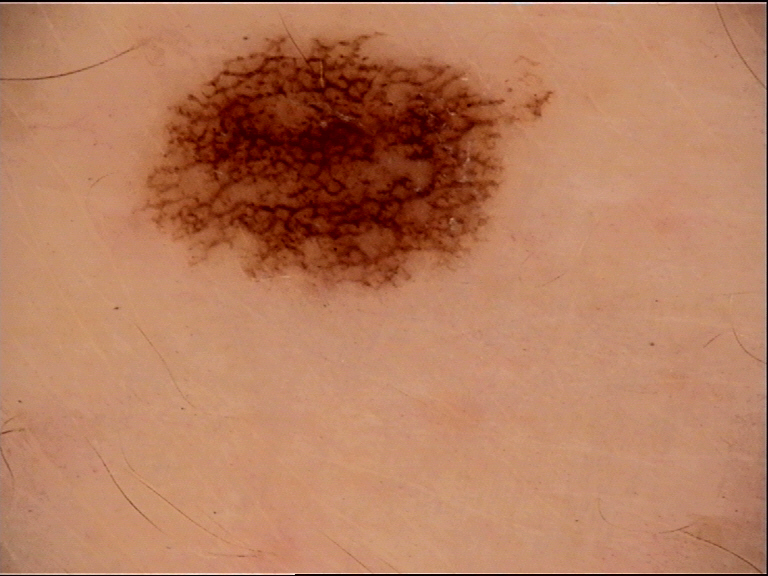modality = dermatoscopy, assessment = dysplastic junctional nevus (expert consensus).